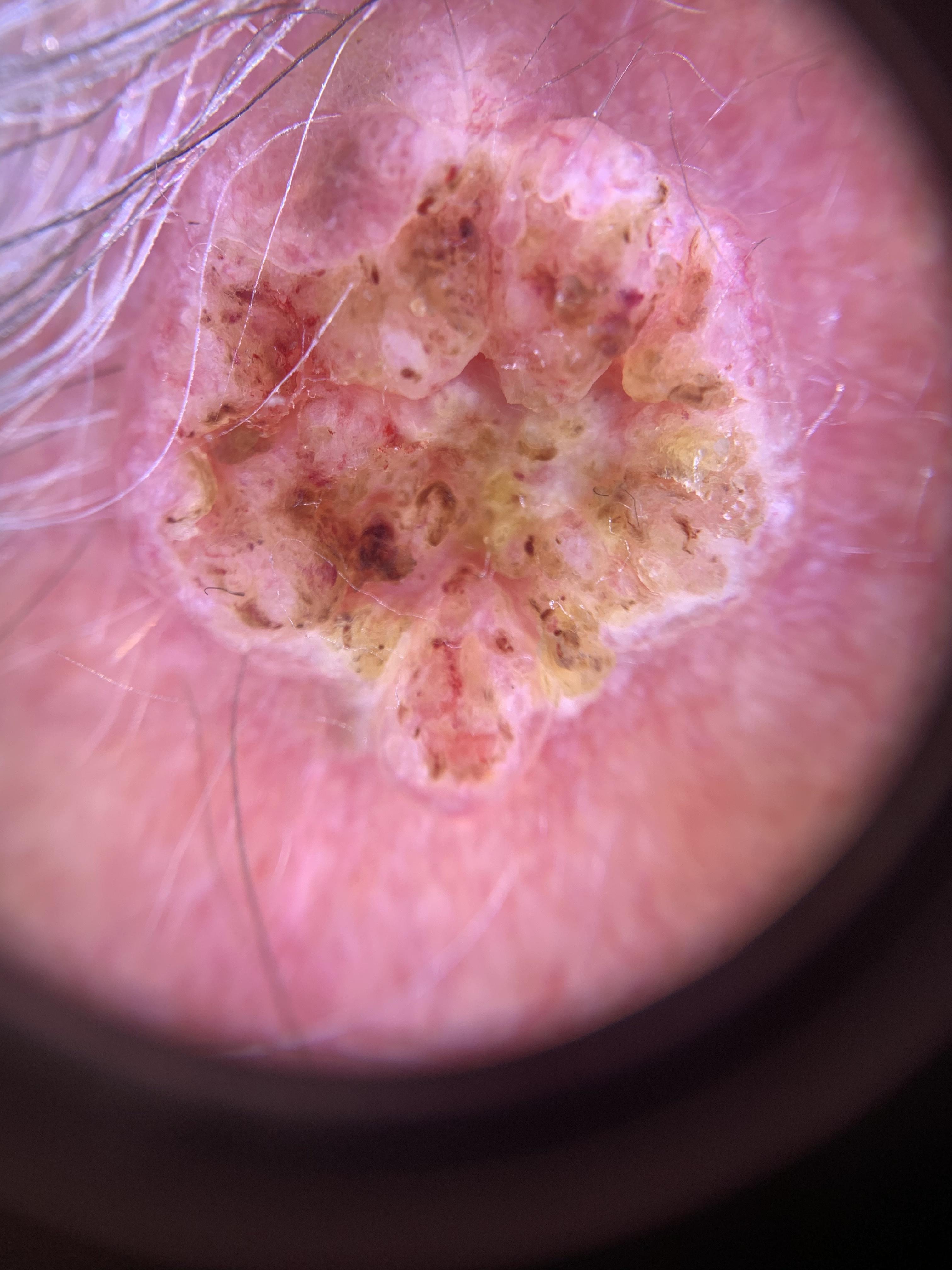Findings: Skin type II. A female subject aged 83 or over. Dermoscopy of a skin lesion. The lesion is on the head or neck. Pathology: On biopsy, the diagnosis was a squamous cell carcinoma.